Located on the leg. An image taken at an angle: 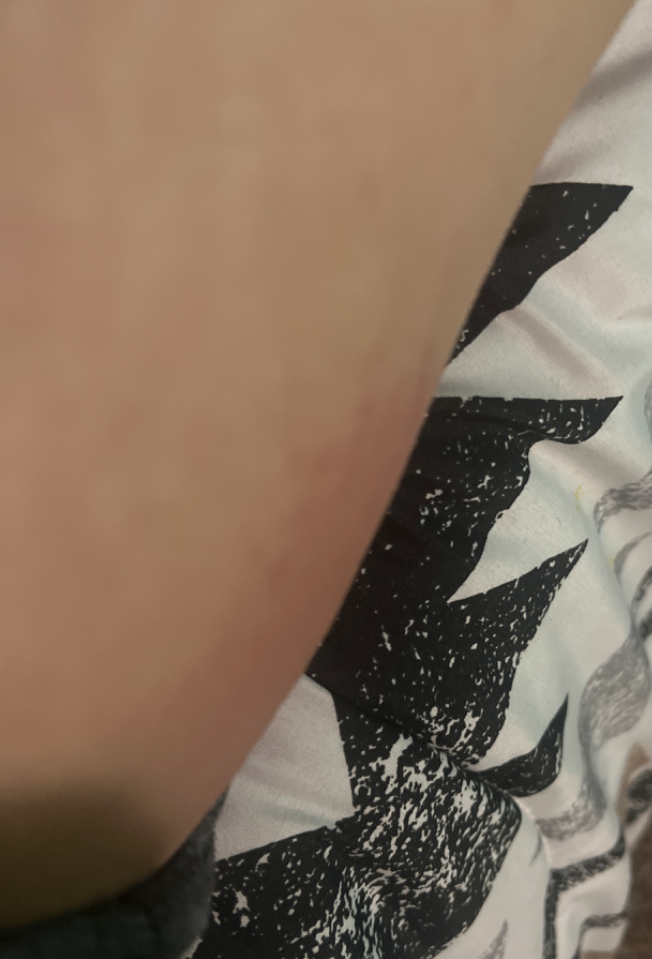The dermatologist could not determine a likely condition from the photograph alone. The patient reports the condition has been present for about one day. The patient described the issue as a rash. The lesion is described as flat. Symptoms reported: pain and burning. The patient reports associated joint pain.